A dermatoscopic image of a skin lesion.
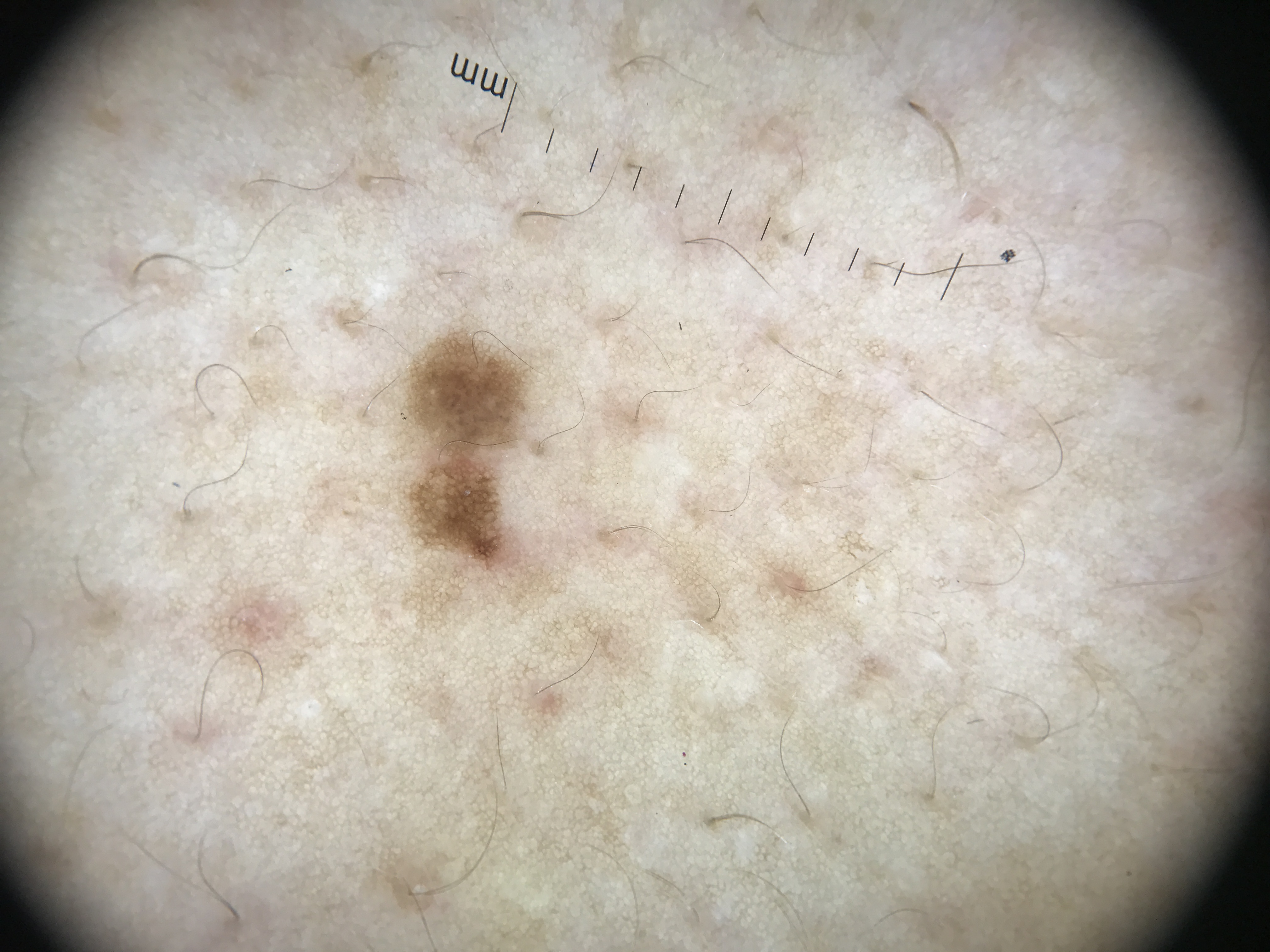<lesion>
  <diagnosis>
    <name>dysplastic junctional nevus</name>
    <code>jd</code>
    <malignancy>benign</malignancy>
    <super_class>melanocytic</super_class>
    <confirmation>expert consensus</confirmation>
  </diagnosis>
</lesion>